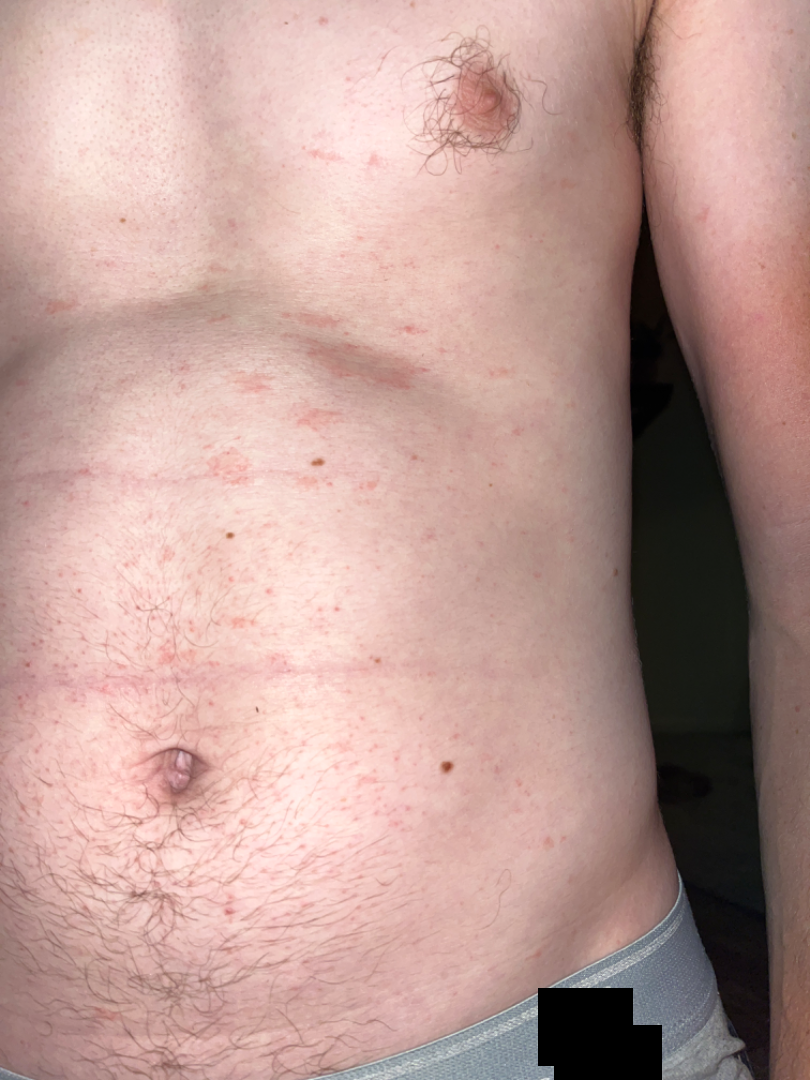assessment=indeterminate from the photograph
body site=front of the torso and back of the torso
subject=male, age 30–39
view=at a distance